Dermoscopy of a skin lesion — 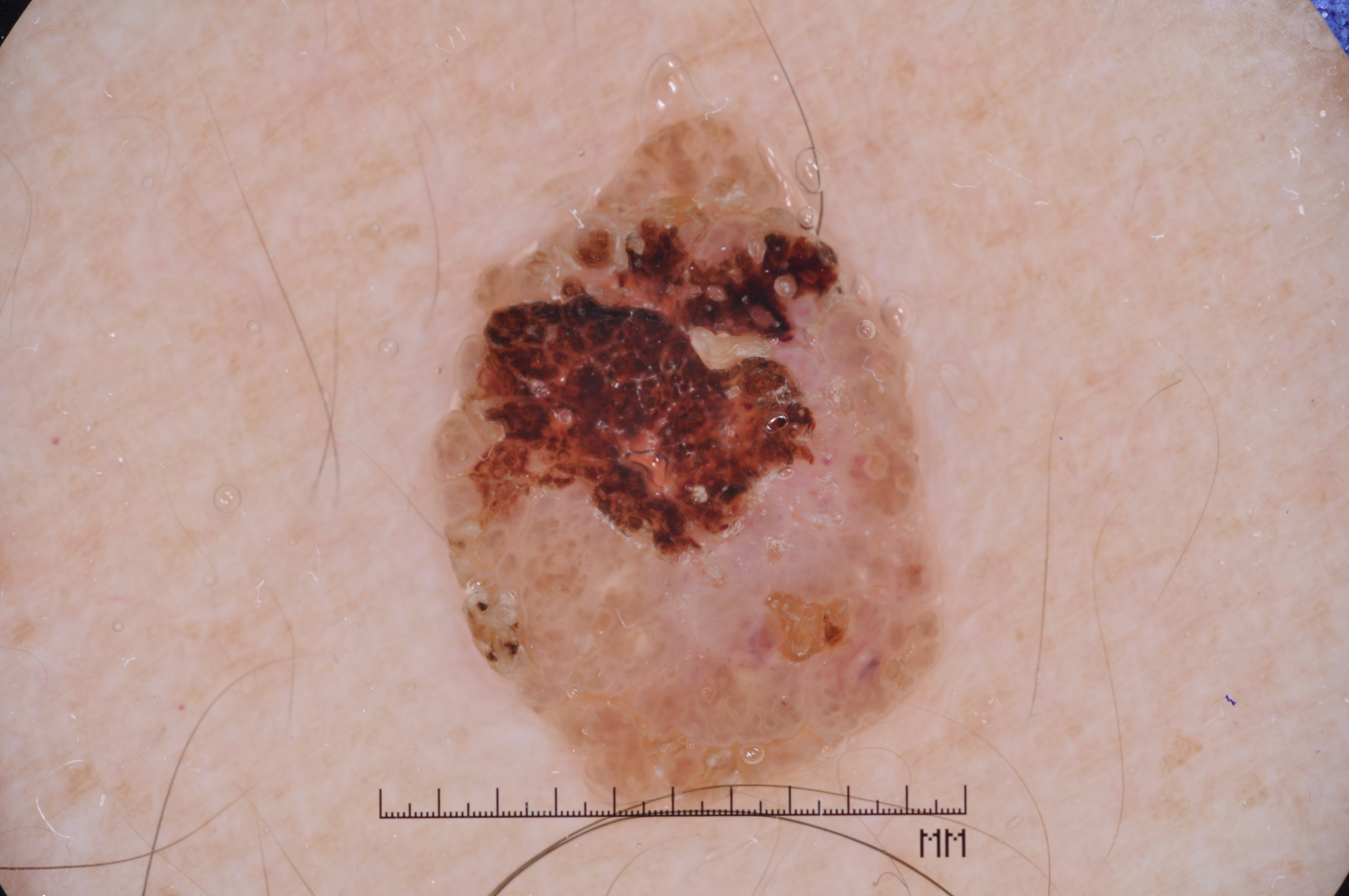Findings: In (x1, y1, x2, y2) order, the lesion is located at bbox(408, 100, 958, 819). Impression: Clinically diagnosed as a seborrheic keratosis, a benign skin lesion.